A dermoscopic close-up of a skin lesion.
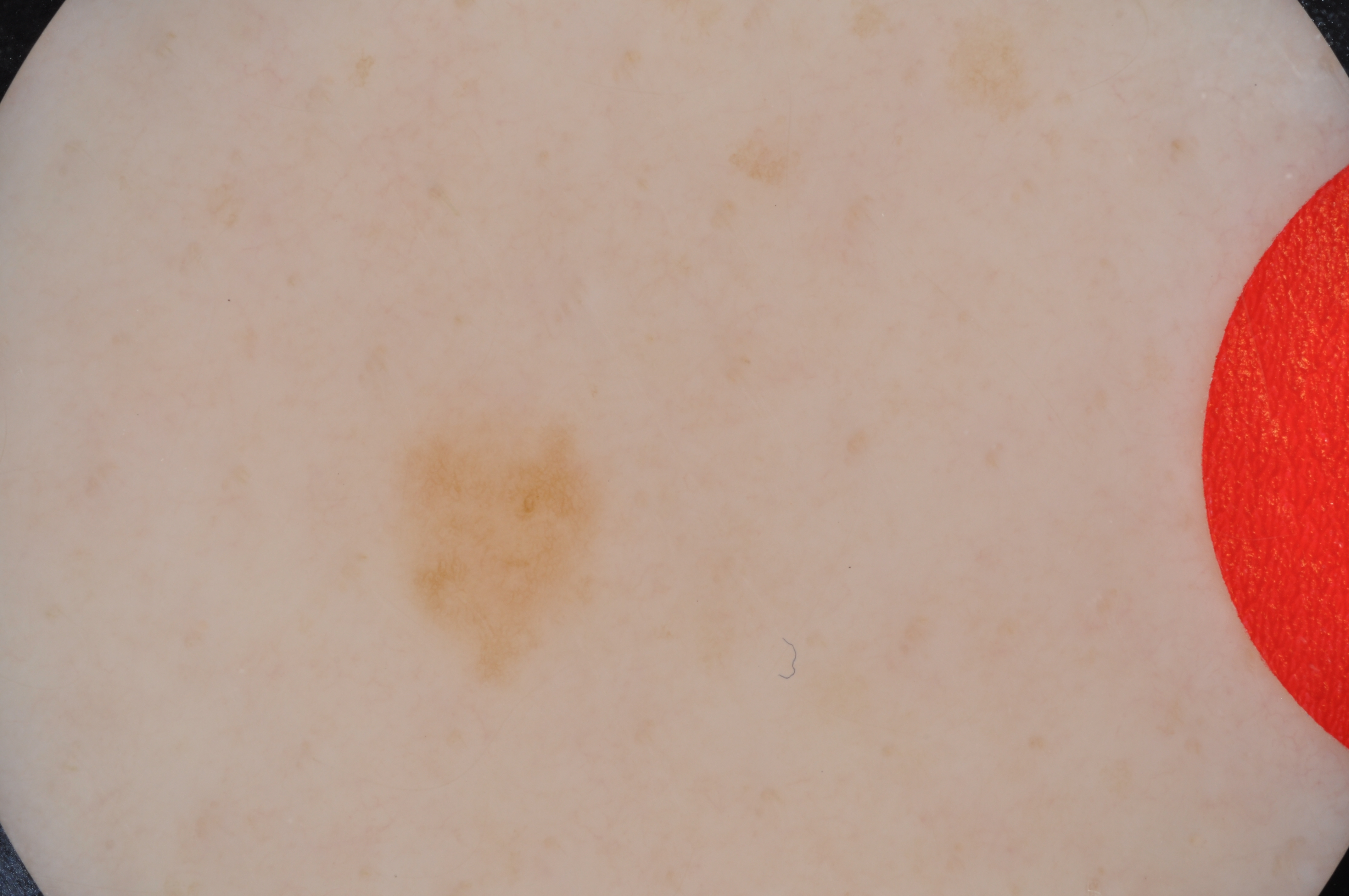The dermoscopic pattern shows neither globules nor streaks.
Lesion location: x1=377 y1=381 x2=640 y2=695.
A small lesion within a wider field of skin.
The lesion was assessed as a benign skin lesion.